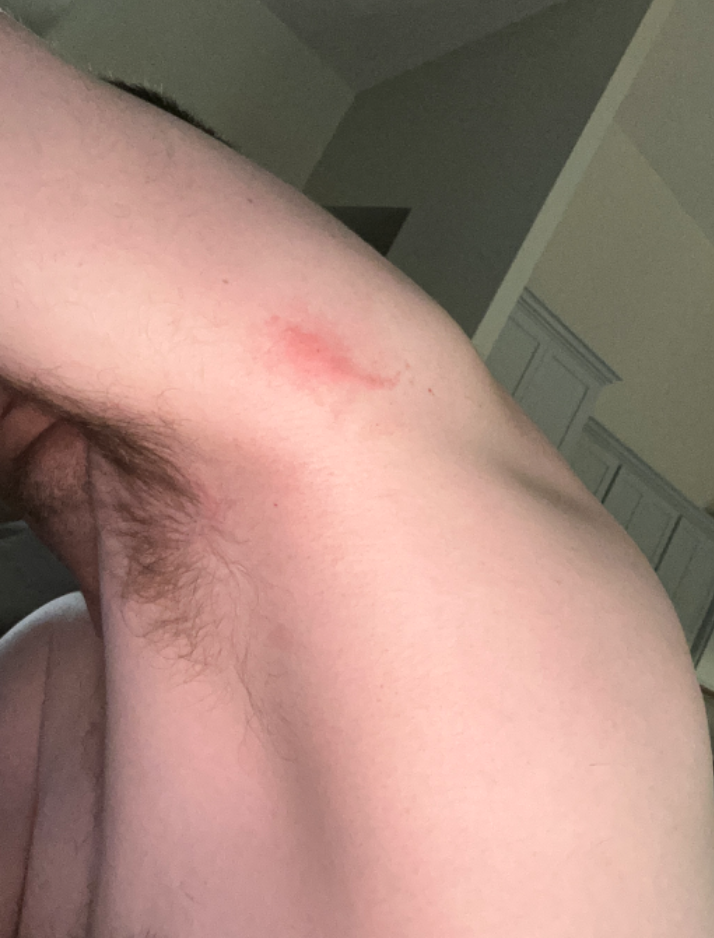Case summary:
– assessment: indeterminate